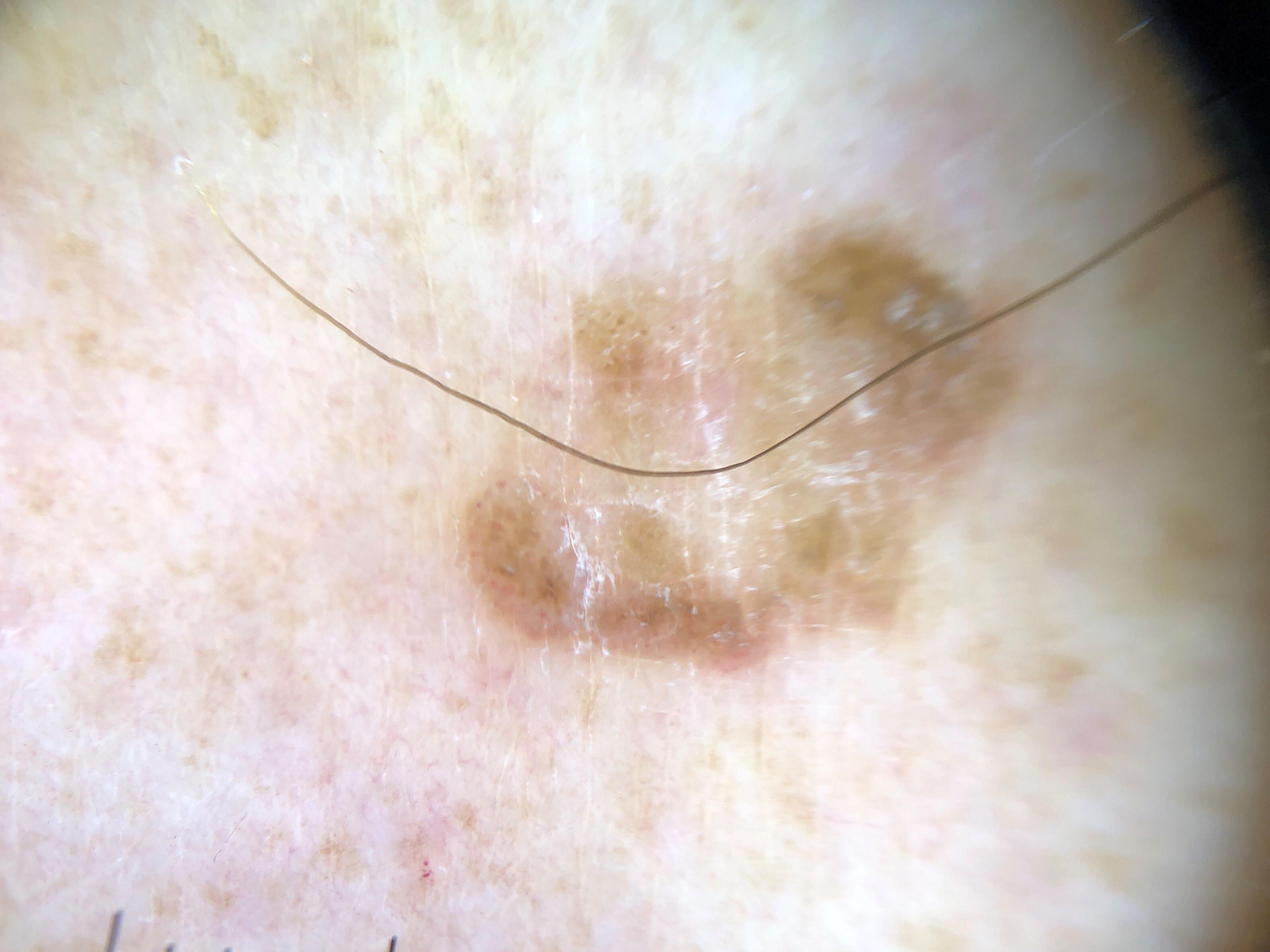A female patient approximately 70 years of age.
The patient is FST II.
A skin lesion imaged with a dermatoscope.
The lesion is on a lower extremity.
The clinical assessment was a lesion of epidermal origin — a seborrheic keratosis.